The back of the hand, back of the torso, arm, top or side of the foot, sole of the foot and leg are involved; this is a close-up image: 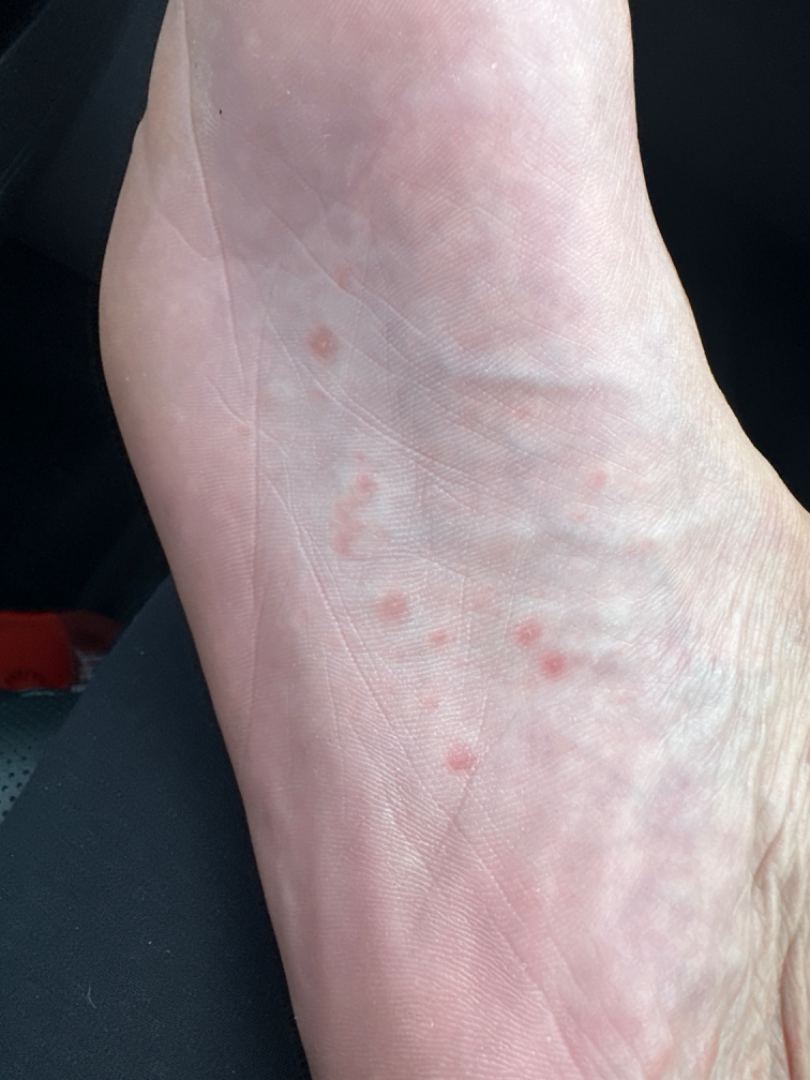differential: Insect Bite